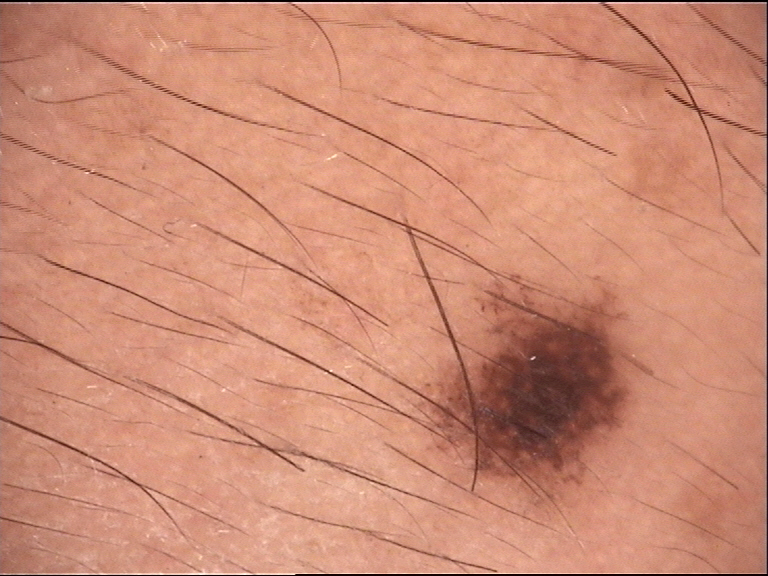A dermoscopy image of a single skin lesion.
The morphology is that of a banal lesion.
The diagnostic label was a compound nevus.